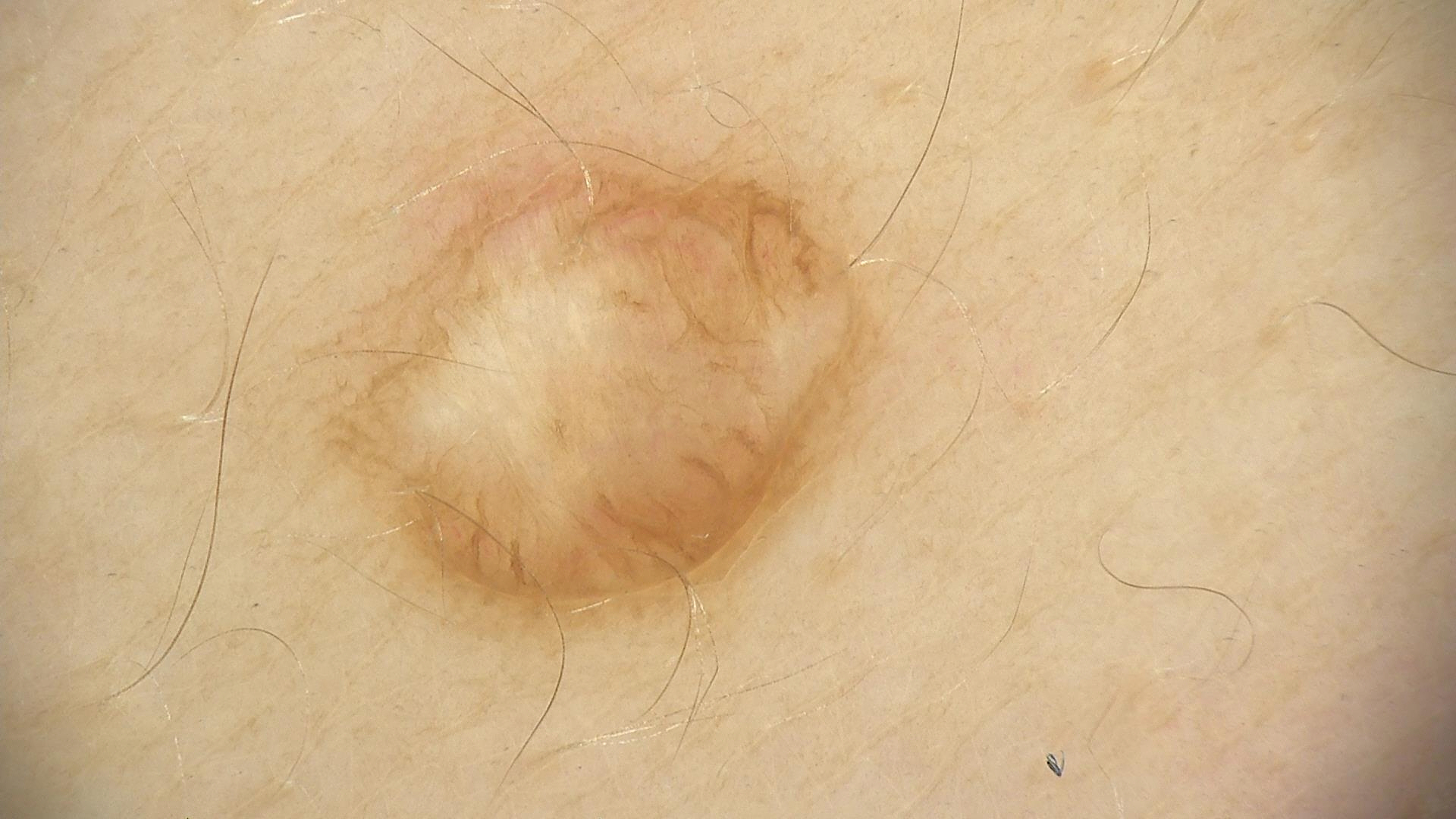The diagnosis was a dermal nevus.